The photo was captured at a distance; the lesion involves the back of the torso: 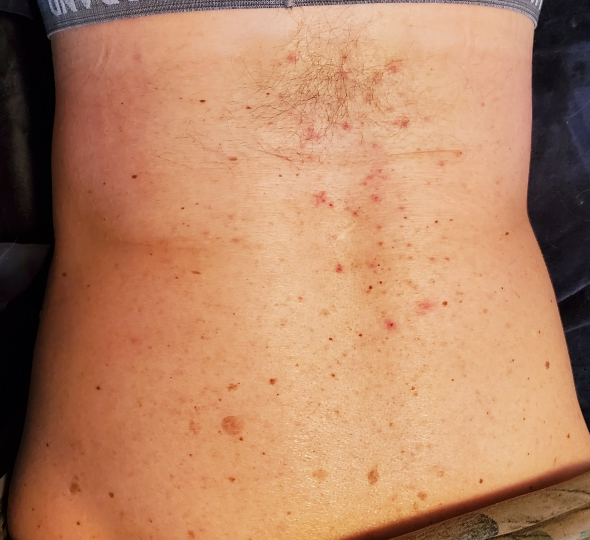The image was not sufficient for the reviewer to characterize the skin condition.